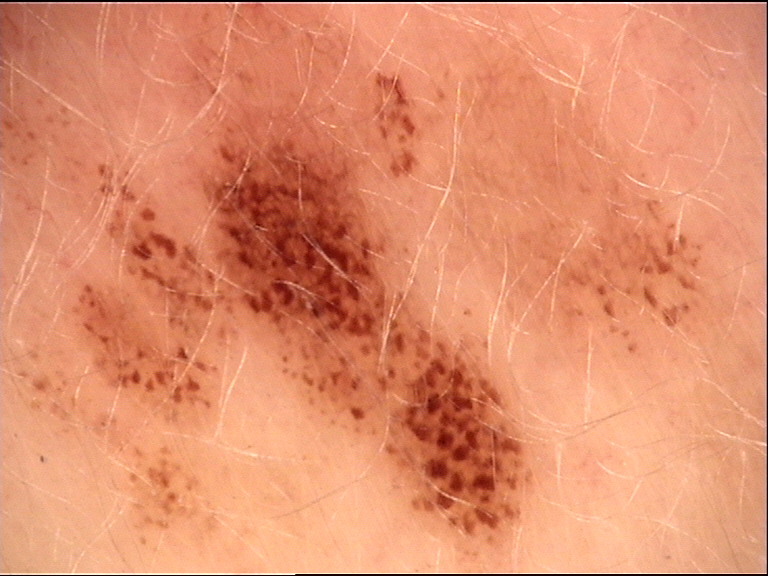A dermoscopy image of a single skin lesion. The architecture is that of a banal lesion. Classified as a congenital junctional nevus.